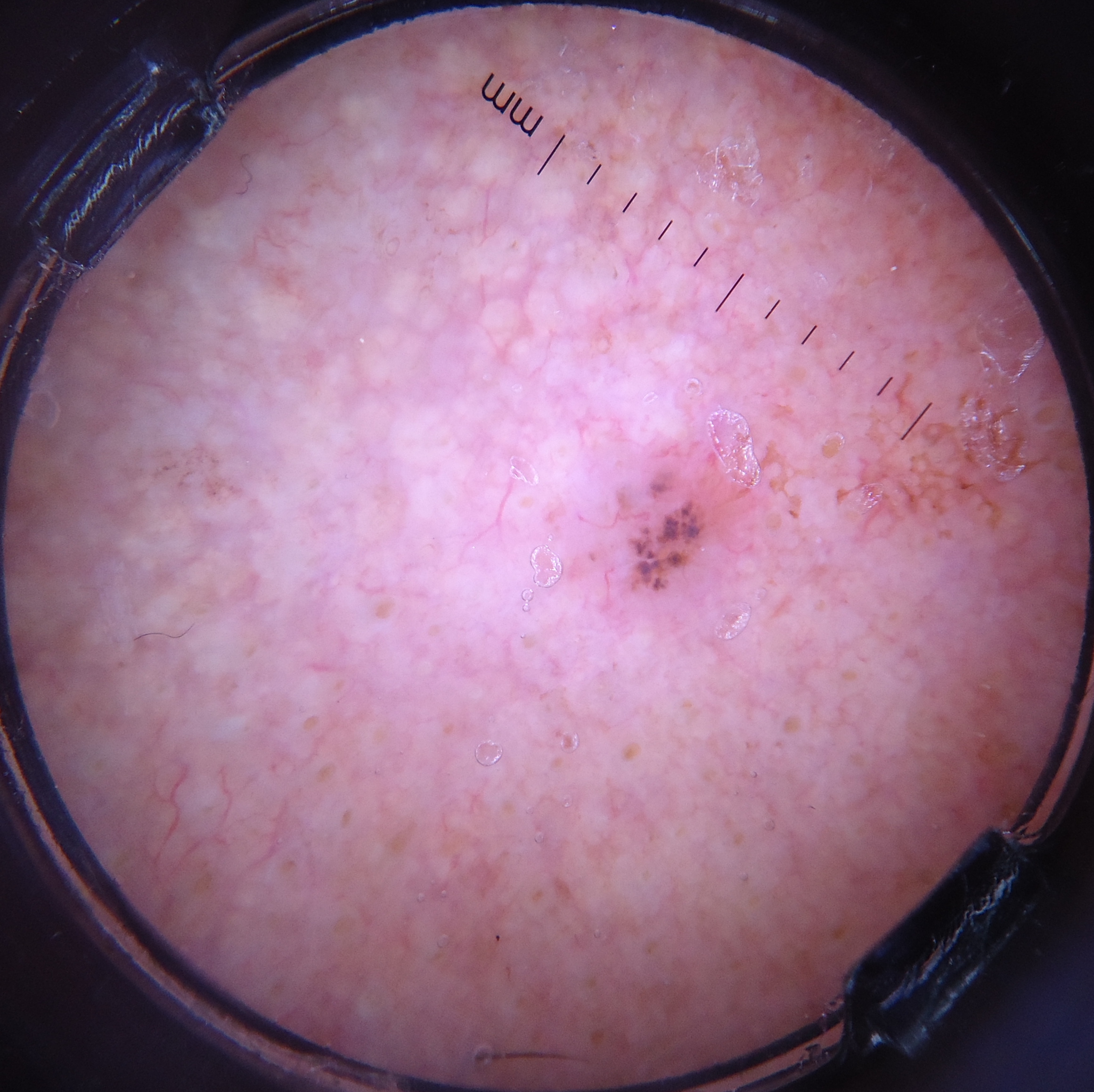Q: How is the lesion classified?
A: keratinocytic
Q: What is the diagnosis?
A: basal cell carcinoma (biopsy-proven)